A skin lesion imaged with a dermatoscope.
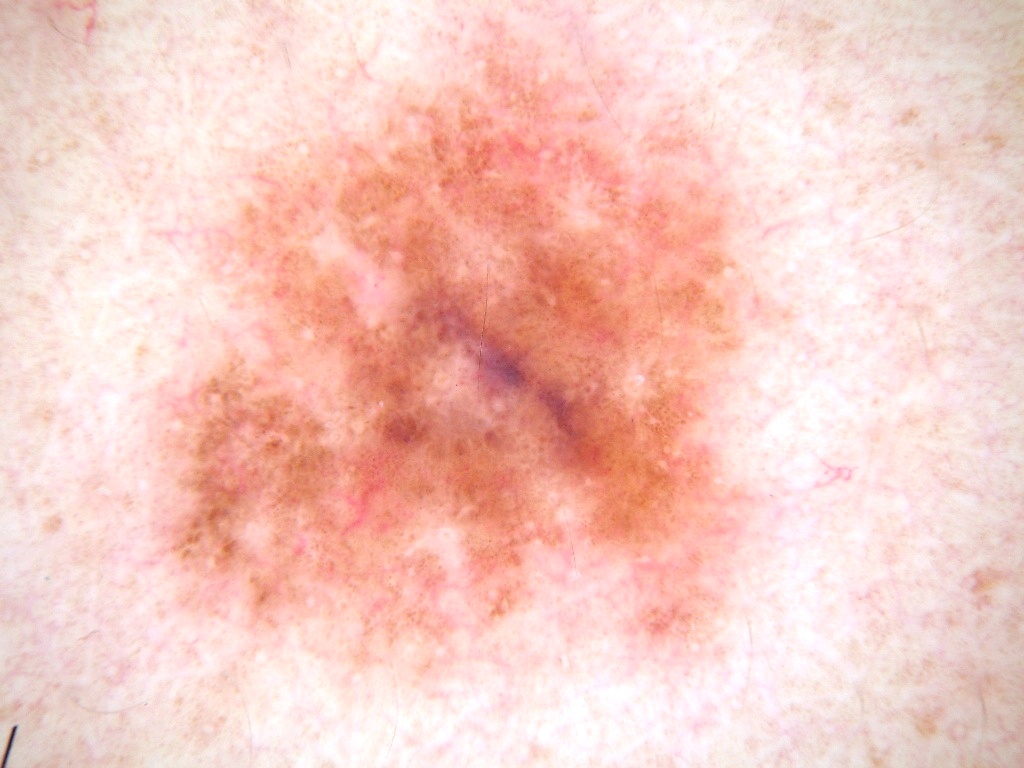  lesion_extent: large
  lesion_location:
    bbox_xyxy:
      - 137
      - 3
      - 812
      - 710
  diagnosis:
    malignancy: benign
    provenance: clinical